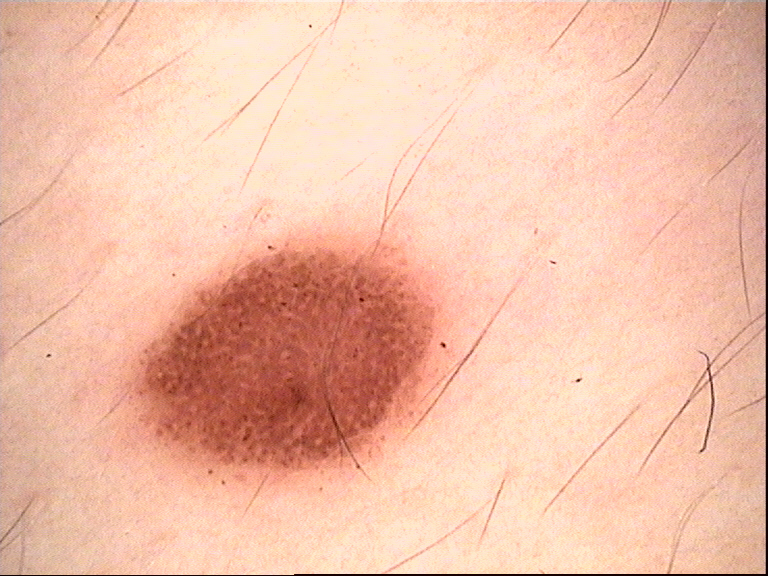<dermoscopy>
  <image>dermoscopy</image>
  <lesion_type>
    <main_class>banal</main_class>
    <pattern>junctional</pattern>
  </lesion_type>
  <diagnosis>
    <name>junctional nevus</name>
    <code>jb</code>
    <malignancy>benign</malignancy>
    <super_class>melanocytic</super_class>
    <confirmation>expert consensus</confirmation>
  </diagnosis>
</dermoscopy>